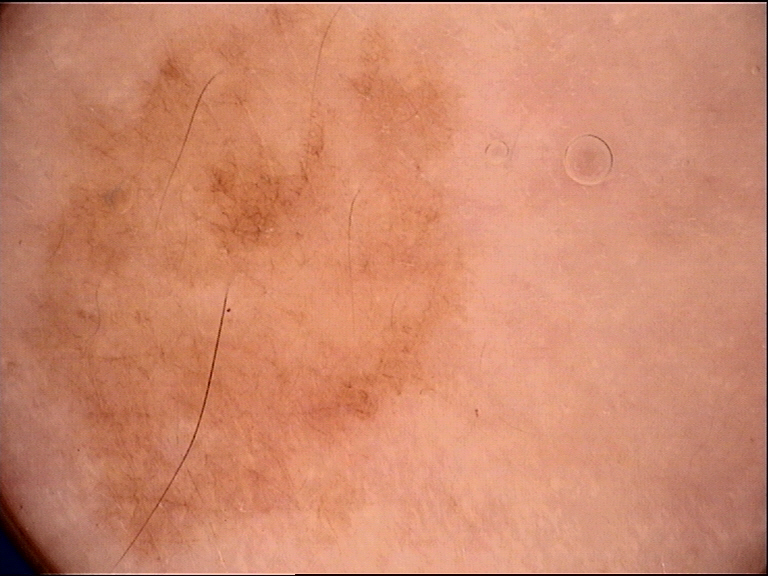– class — dysplastic junctional nevus (expert consensus)